A dermoscopy image of a single skin lesion, the subject is a female aged around 40.
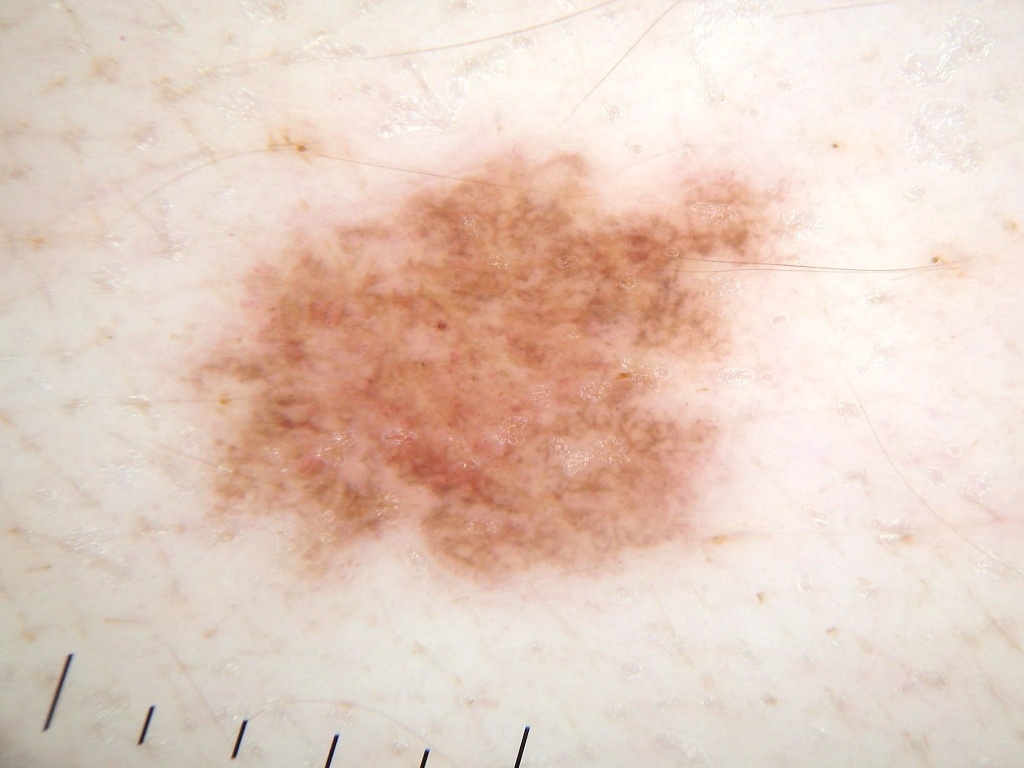  lesion_location:
    bbox_xyxy:
      - 156
      - 152
      - 772
      - 598
  dermoscopic_features:
    present:
      - globules
      - pigment network
    absent:
      - streaks
      - negative network
      - milia-like cysts
  diagnosis:
    name: melanocytic nevus
    malignancy: benign
    lineage: melanocytic
    provenance: clinical